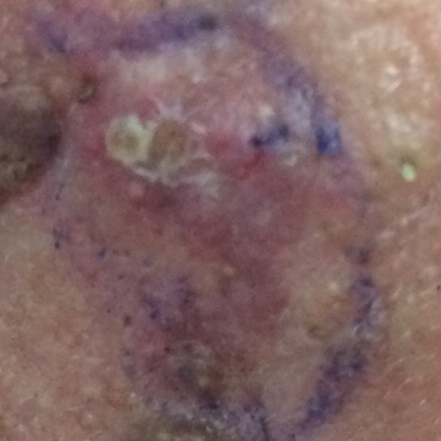image=clinical photo
subject=male, age 43
body site=the face
pathology=basal cell carcinoma (biopsy-proven)